Fitzpatrick II. A male subject aged 73 to 77. A dermoscopic image of a skin lesion — 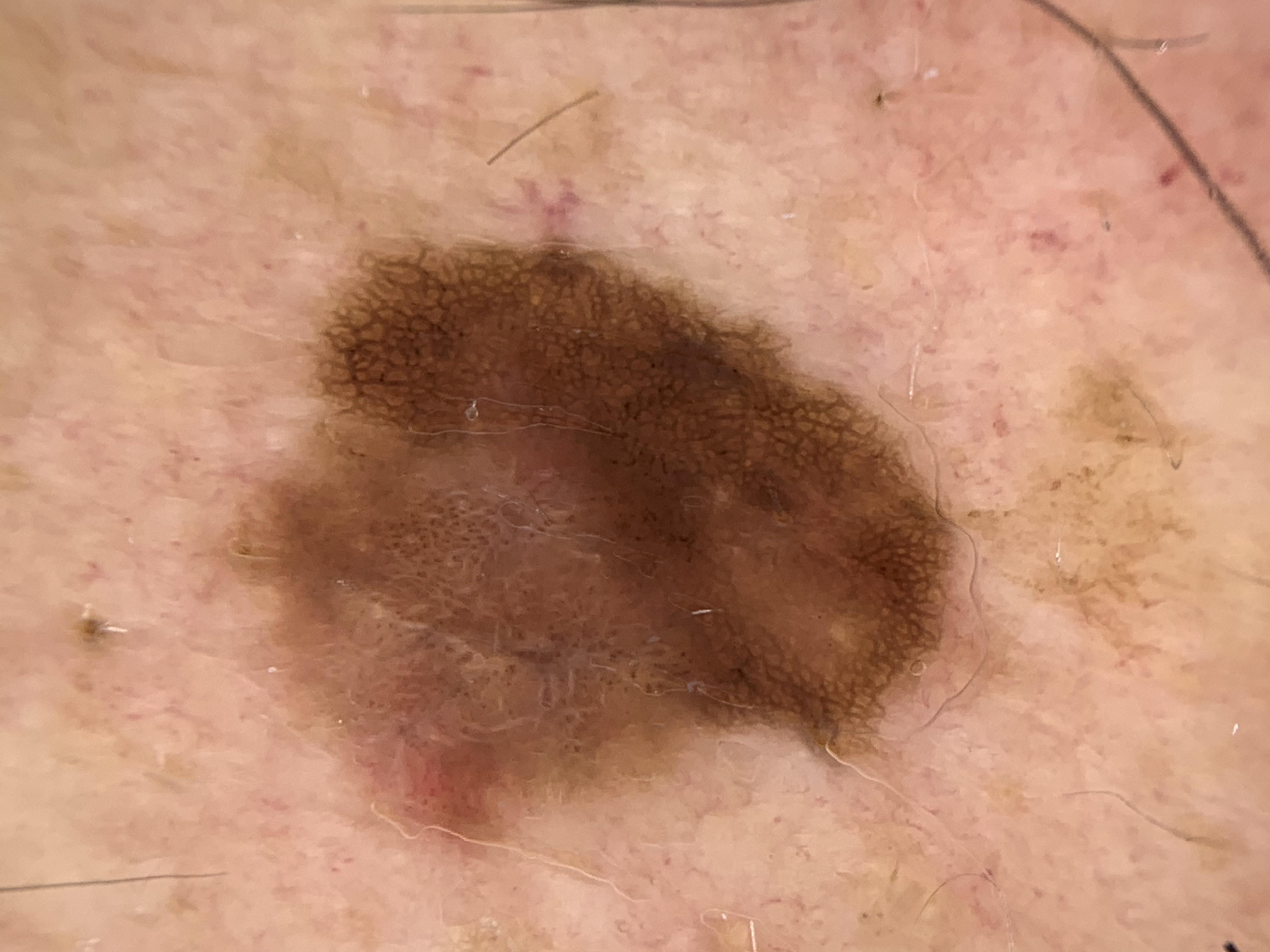anatomic site: the head or neck; diagnosis: Nevus (biopsy-proven).